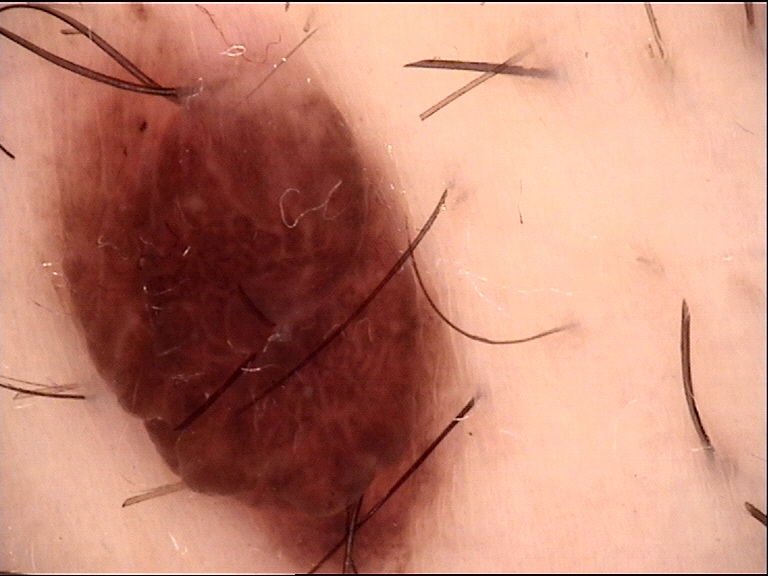Summary:
A dermoscopic photograph of a skin lesion.
Conclusion:
The diagnostic label was a banal lesion — a compound nevus.